A dermatoscopic image of a skin lesion; the subject is a female aged approximately 75: 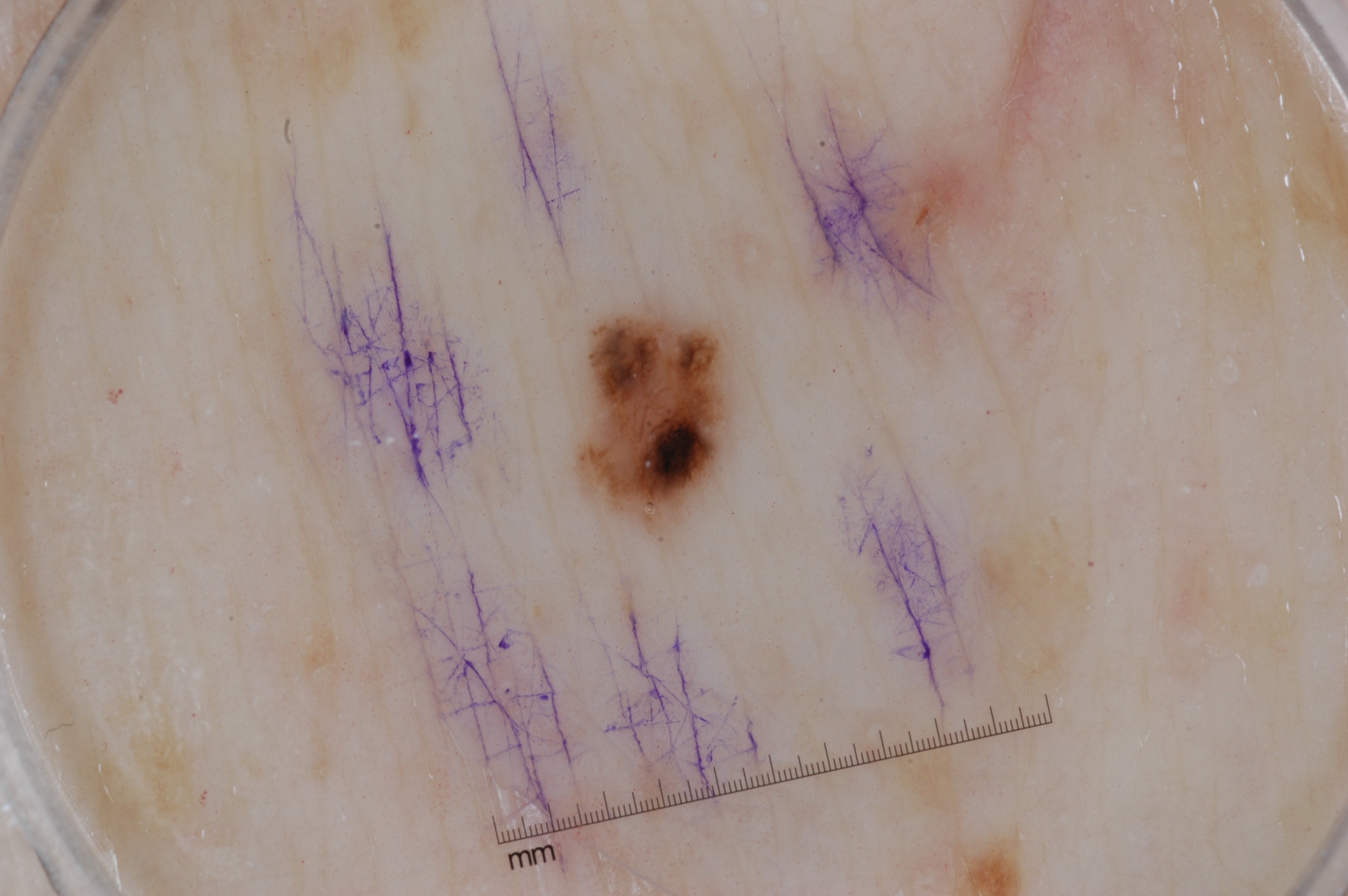Dermoscopically, the lesion shows pigment network and milia-like cysts; no negative network or streaks. The lesion's extent is x1=567 y1=306 x2=751 y2=532. Clinically diagnosed as a melanocytic nevus, a benign skin lesion.